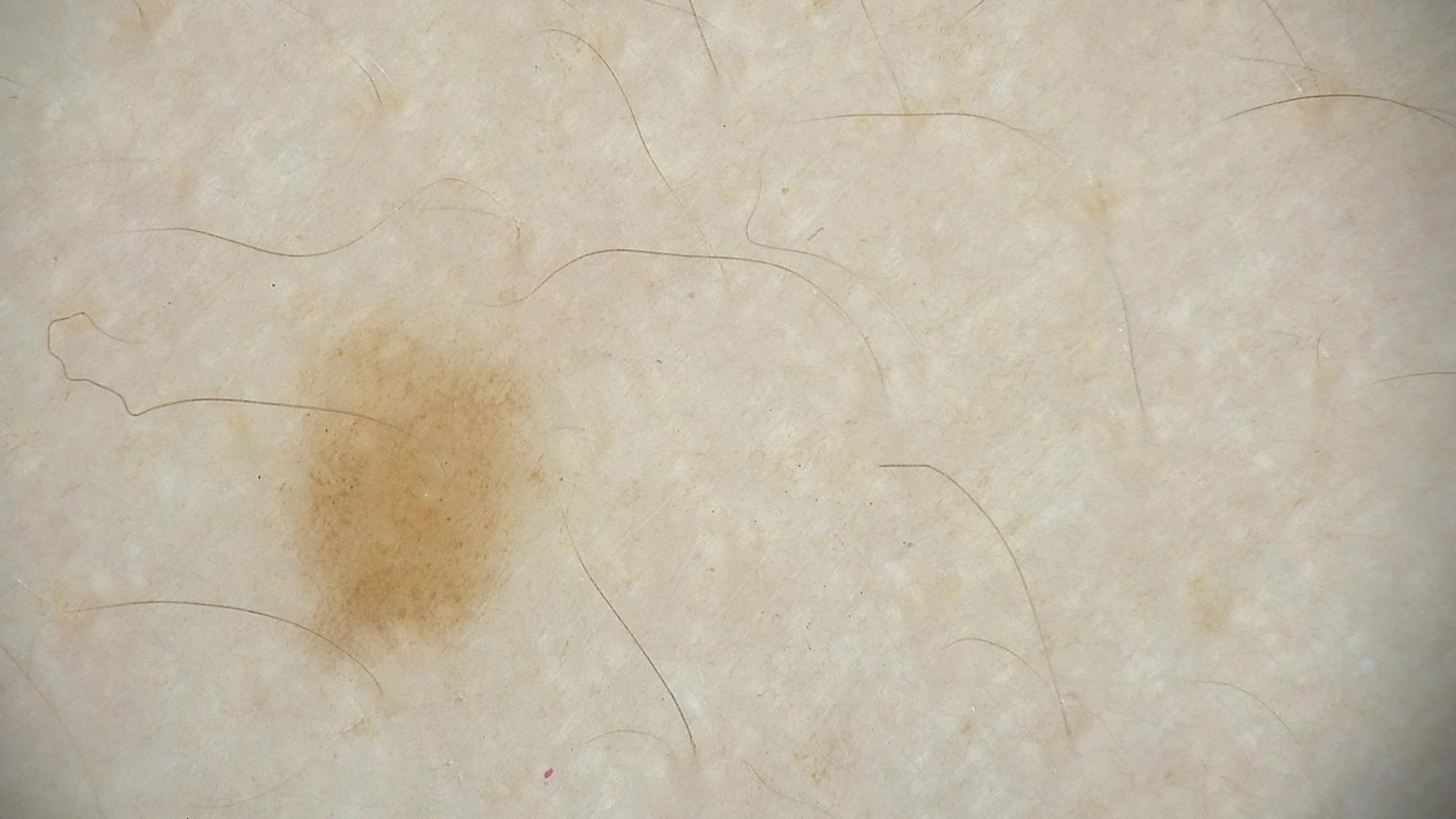Findings:
A dermoscopy image of a single skin lesion.
Conclusion:
The diagnostic label was a benign lesion — a dysplastic junctional nevus.